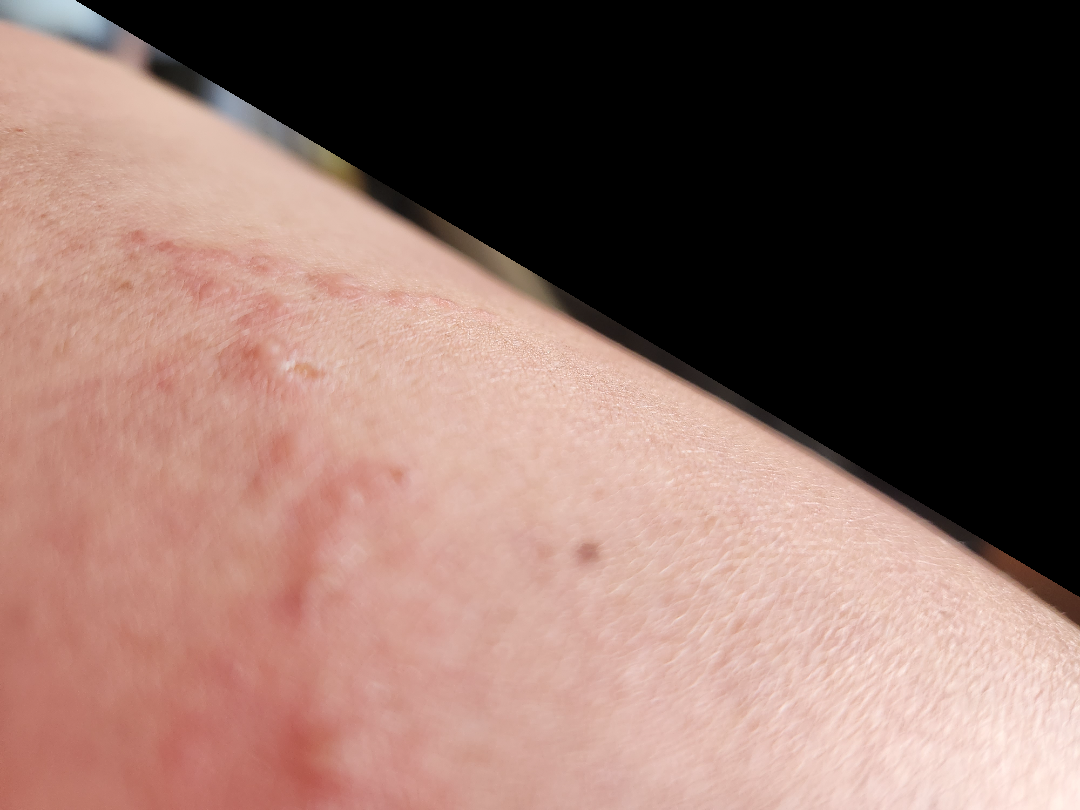| field | value |
|---|---|
| location | leg |
| shot type | at an angle |
| dermatologist impression | the differential is split between Cutaneous larva migrans, Herpes Simplex and Allergic Contact Dermatitis |